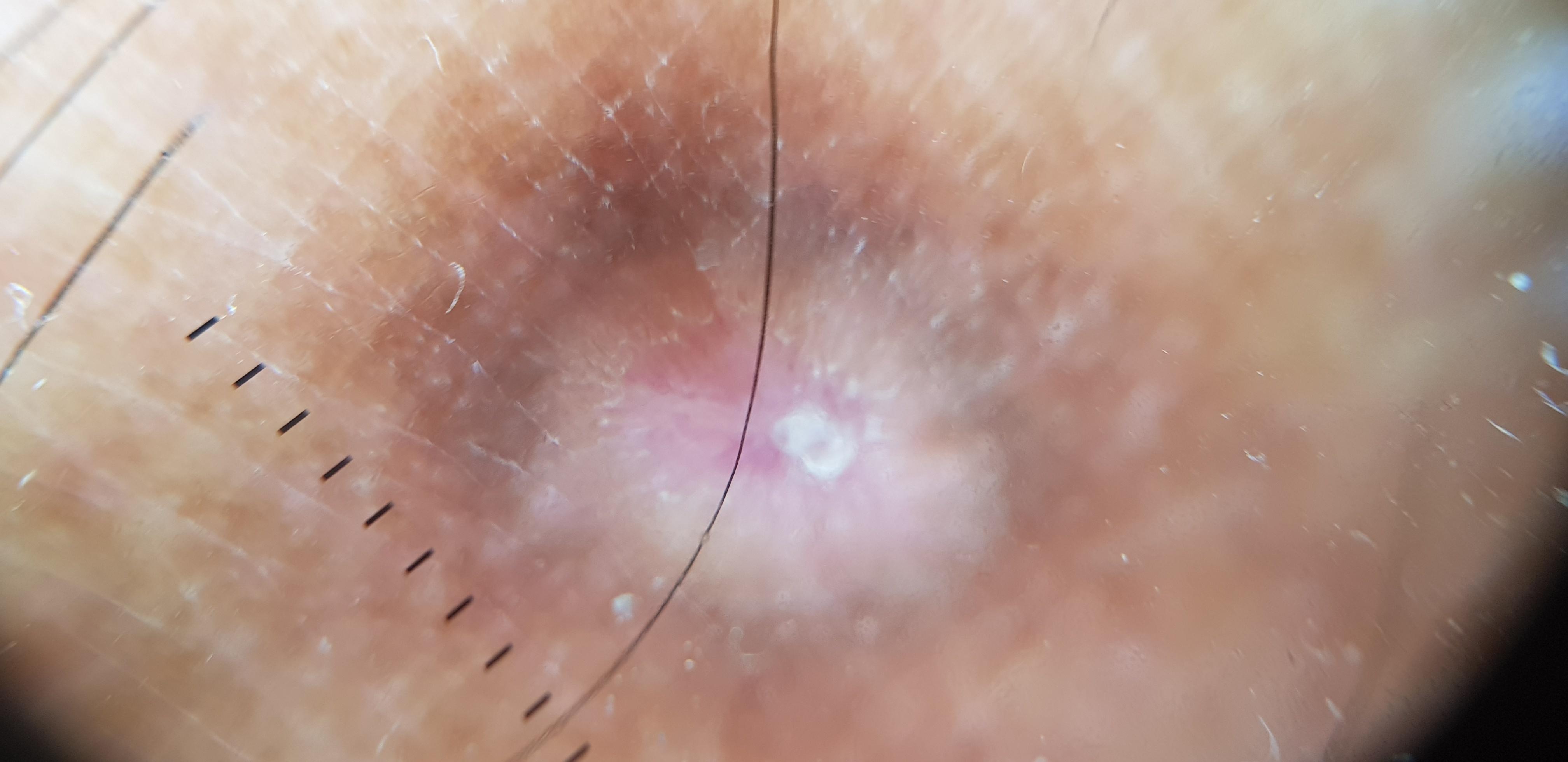{"patient": {"age_approx": 65, "sex": "male"}, "skin_type": "II", "image": "dermoscopic image", "lesion_location": {"region": "a lower extremity"}, "diagnosis": {"name": "Dermatofibroma", "malignancy": "benign", "confirmation": "histopathology", "lineage": "fibro-histiocytic"}}